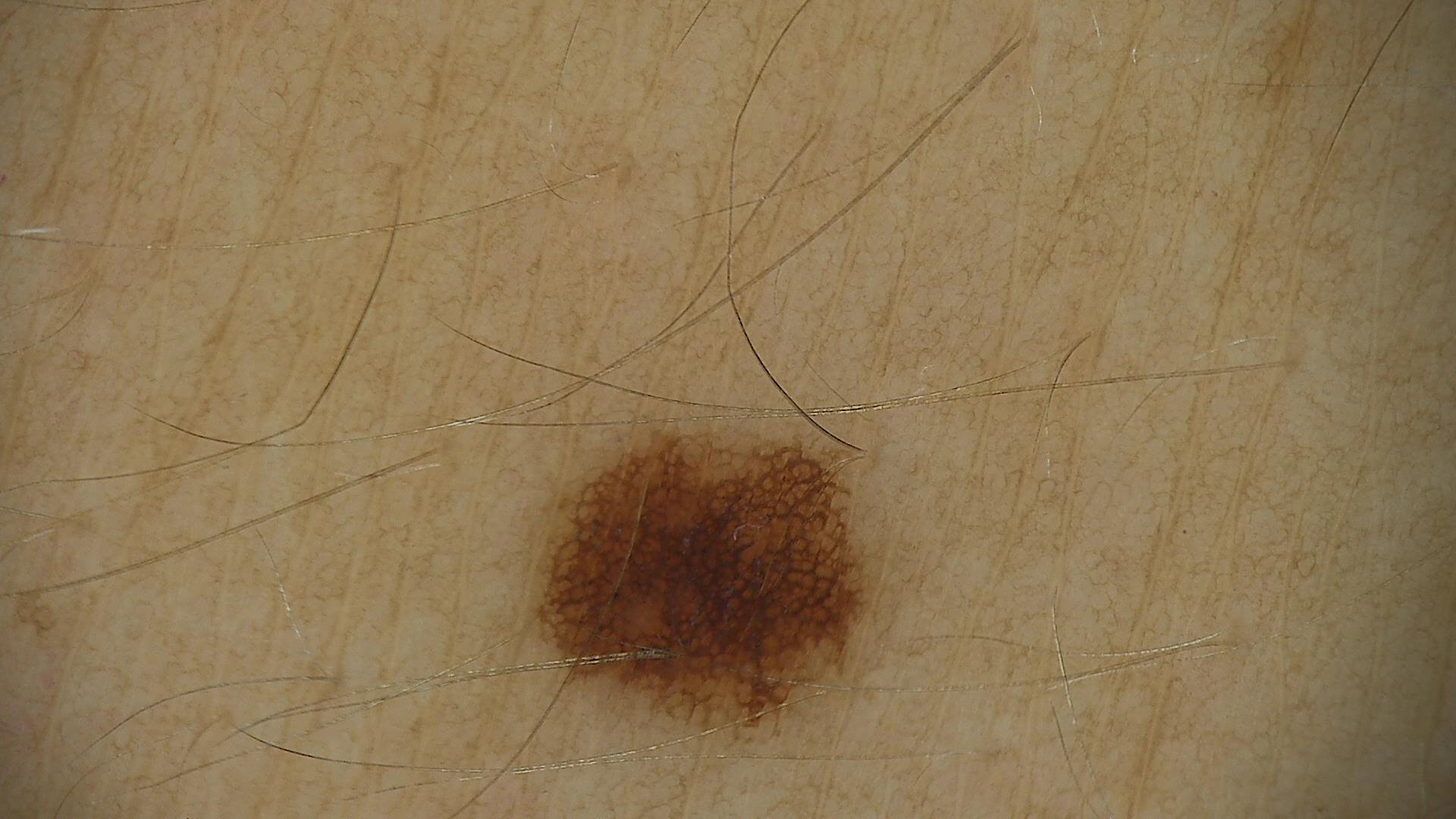A skin lesion imaged with a dermatoscope.
The diagnostic label was a dysplastic junctional nevus.